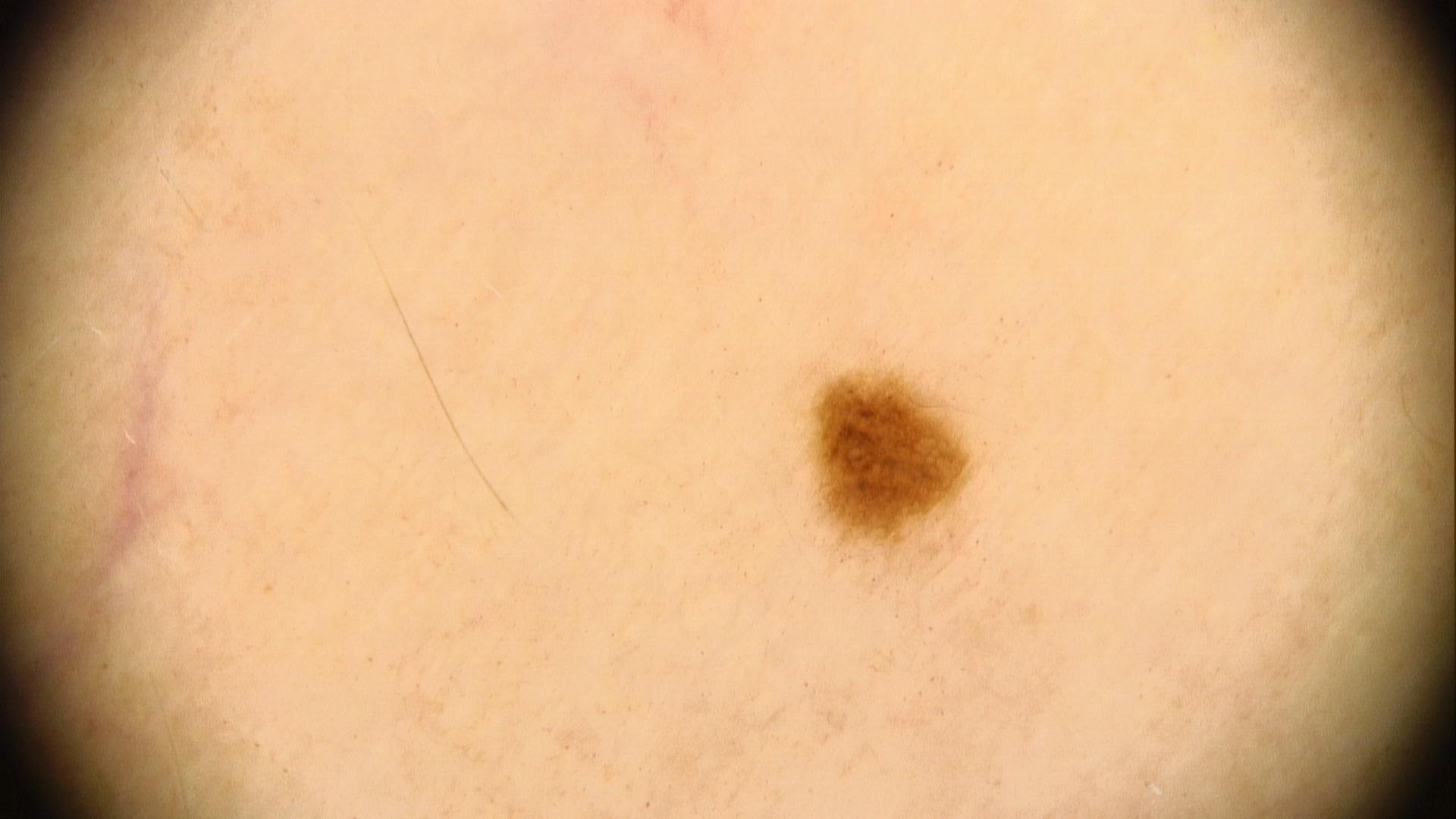melanoma history = no first-degree relative with melanoma and no prior melanoma; imaging = dermoscopy; subject = female, aged 53 to 57; skin phototype = IV; anatomic site = a lower extremity; assessment = Nevus.